The lesion involves the arm · no associated systemic symptoms reported · the contributor reports the lesion is raised or bumpy · female subject, age 40–49 · Fitzpatrick I · the photograph was taken at an angle · the contributor reports the condition has been present for one to four weeks: 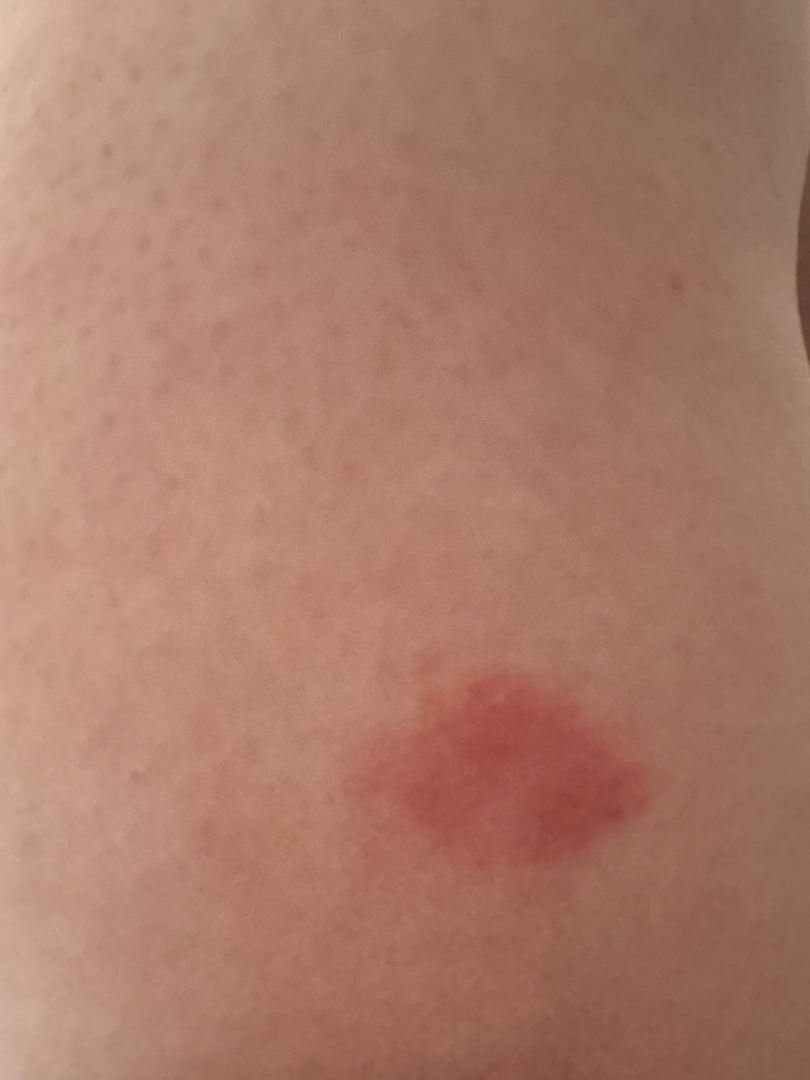<dermatology_case>
<differential>
  <tied_lead>Pigmented purpuric eruption, Eczema, Allergic Contact Dermatitis</tied_lead>
</differential>
</dermatology_case>